The patient notes the lesion is raised or bumpy · the patient considered this skin that appeared healthy to them · the condition has been present for one to four weeks · the photograph is a close-up of the affected area · the patient notes bothersome appearance · the head or neck is involved · the patient is a female aged 40–49 · the patient also reports fatigue — 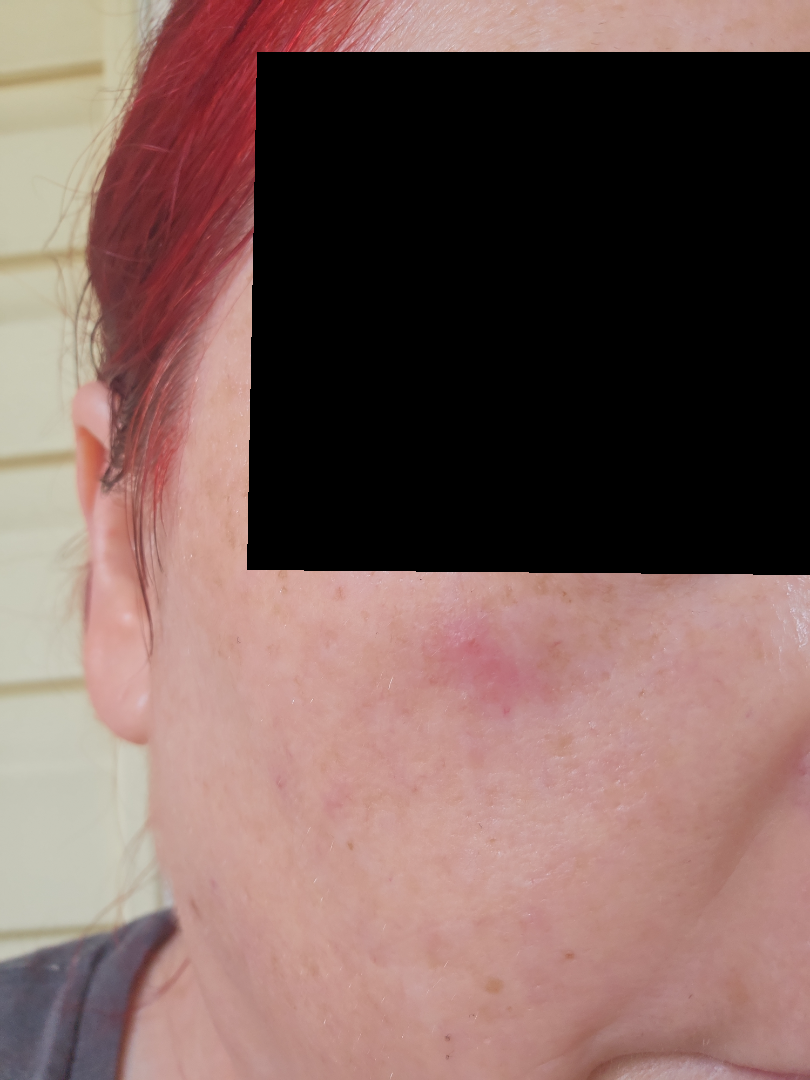Findings: On dermatologist assessment of the image: Hemangioma (55%); Rosacea (27%); Acne (18%).